A close-up photograph; the contributor reports the lesion is flat; the contributor is female; self-categorized by the patient as a rash; the arm, leg, head or neck, front of the torso, palm and back of the torso are involved; the lesion is associated with enlargement and bothersome appearance — 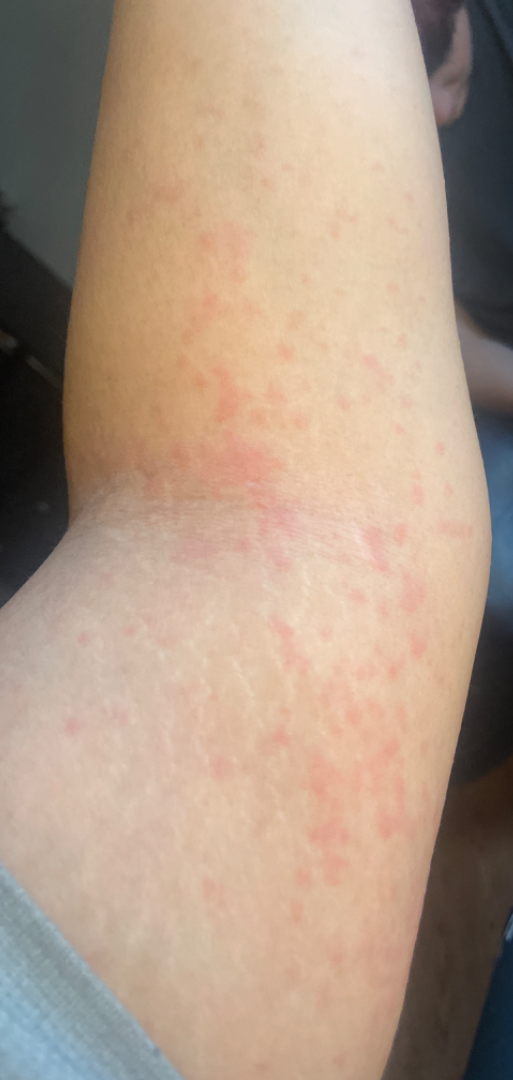On dermatologist assessment of the image, the impression is Urticaria.